A dermoscopic view of a skin lesion:
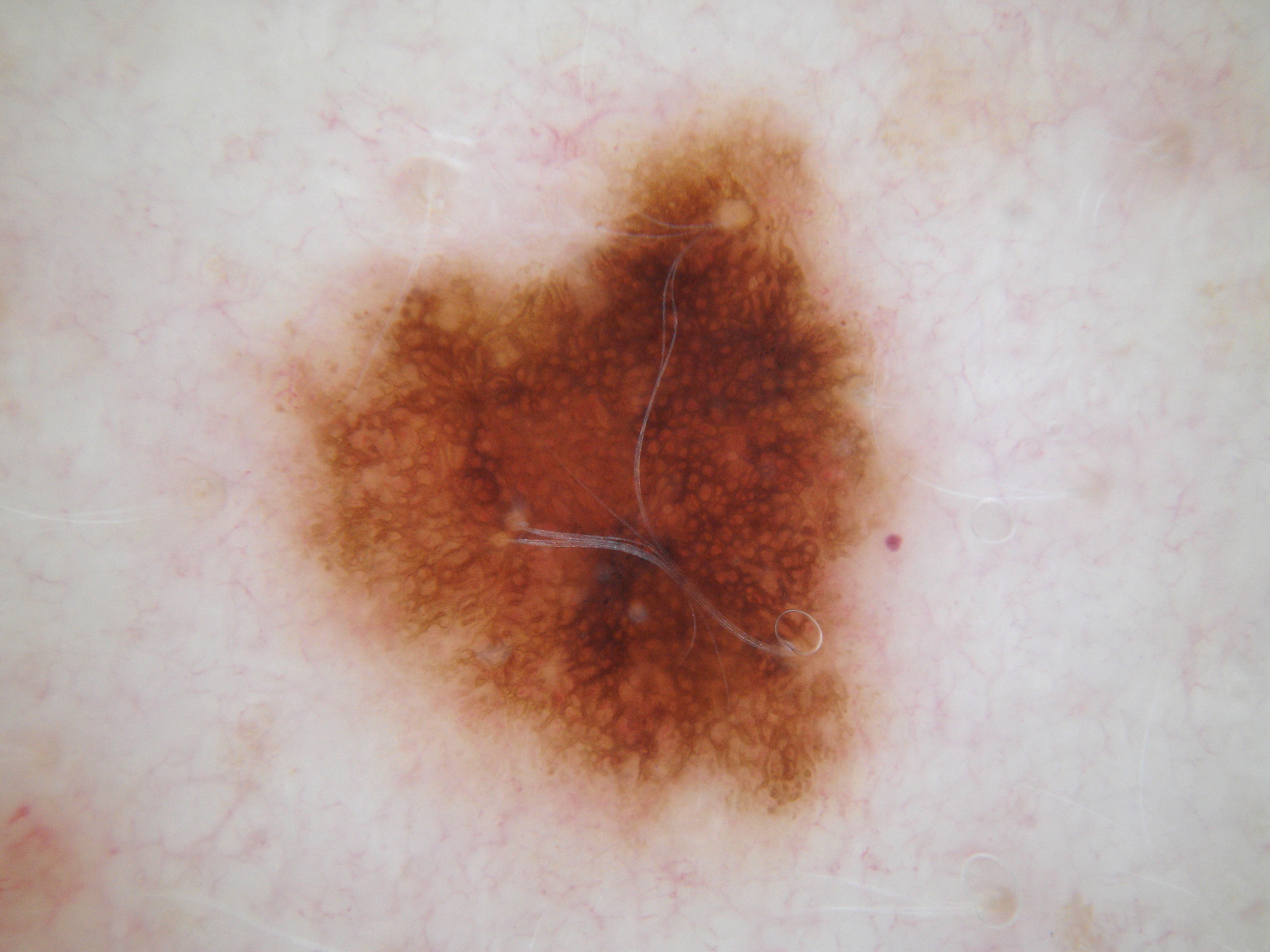lesion bbox — 254, 100, 912, 856; extent — ~27% of the field; dermoscopic findings — streaks, globules, and pigment network; assessment — a melanocytic nevus.